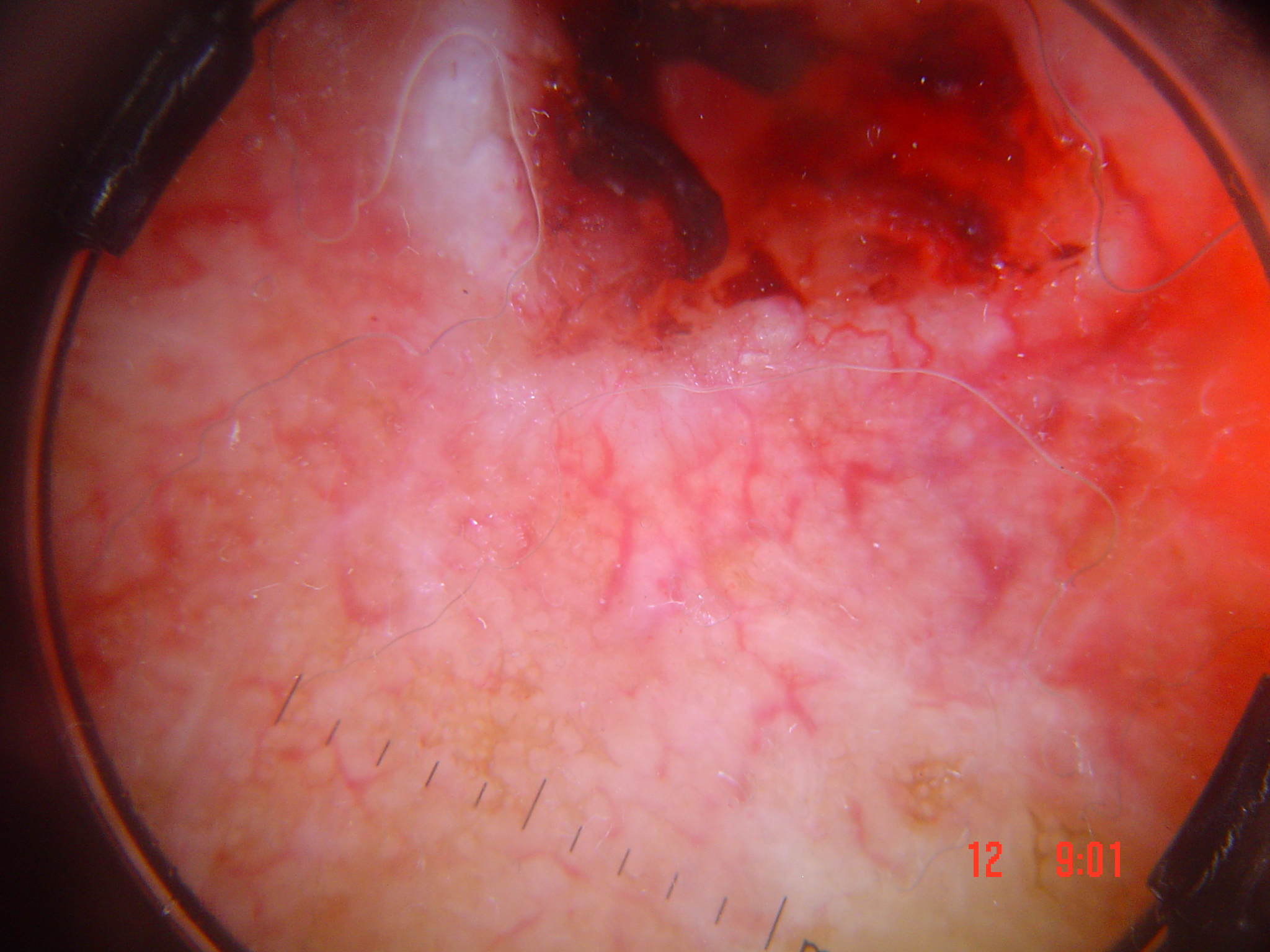A dermoscopic close-up of a skin lesion.
This is a keratinocytic lesion.
The biopsy diagnosis was a skin cancer — a squamous cell carcinoma.